A dermoscopic close-up of a skin lesion.
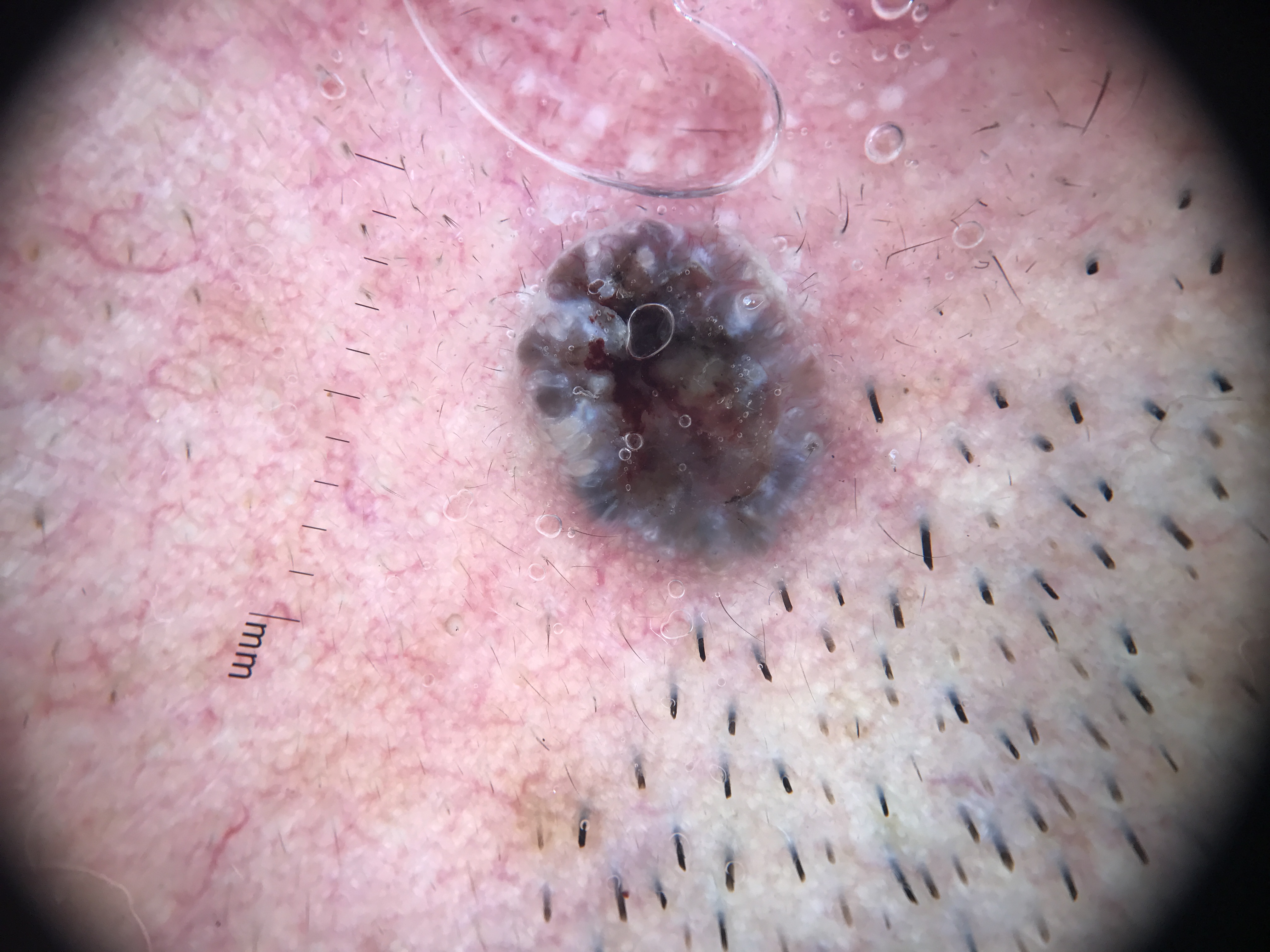Case:
The architecture is that of a keratinocytic lesion.
Diagnosis:
Confirmed on histopathology as a basal cell carcinoma.